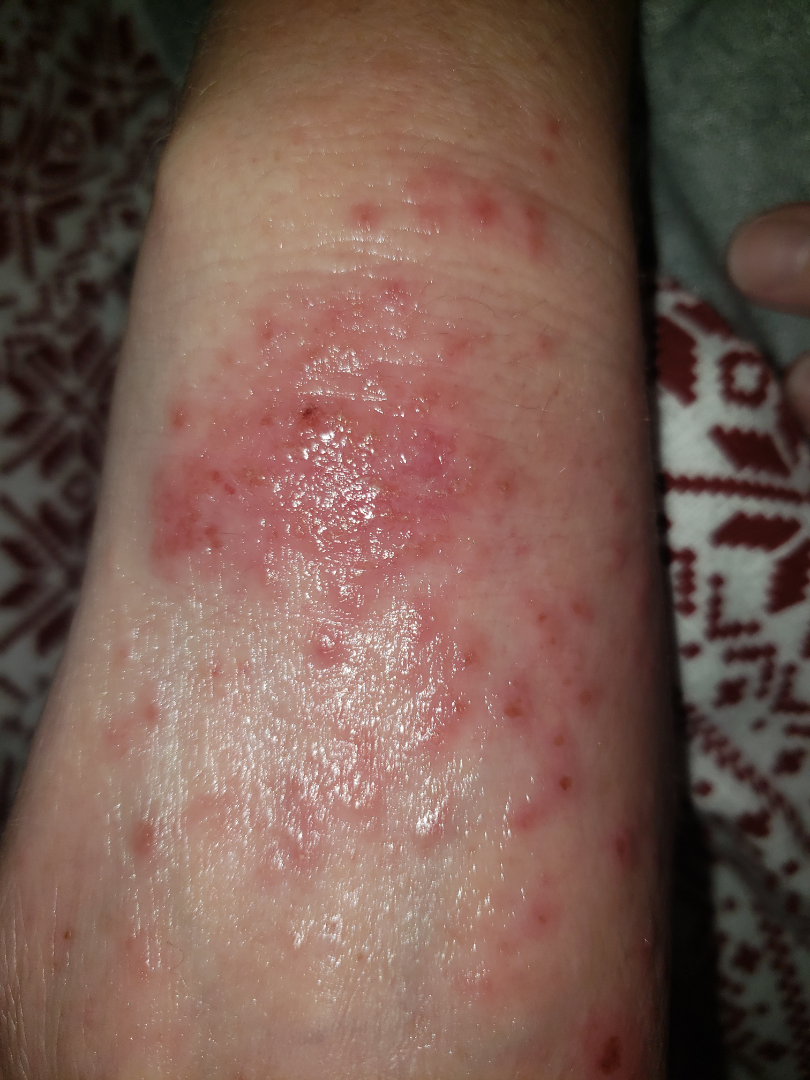Patient information: This is a close-up image. The patient indicates associated shortness of breath, chills and fever. Self-categorized by the patient as a rash. The patient is 40–49, female. Reported duration is one to three months. The patient indicates the lesion is raised or bumpy, rough or flaky and fluid-filled. Located on the back of the hand. The lesion is associated with pain, itching and burning. Review: On teledermatology review, Allergic Contact Dermatitis and Herpes Simplex were each considered, in no particular order; less likely is Infected eczema.